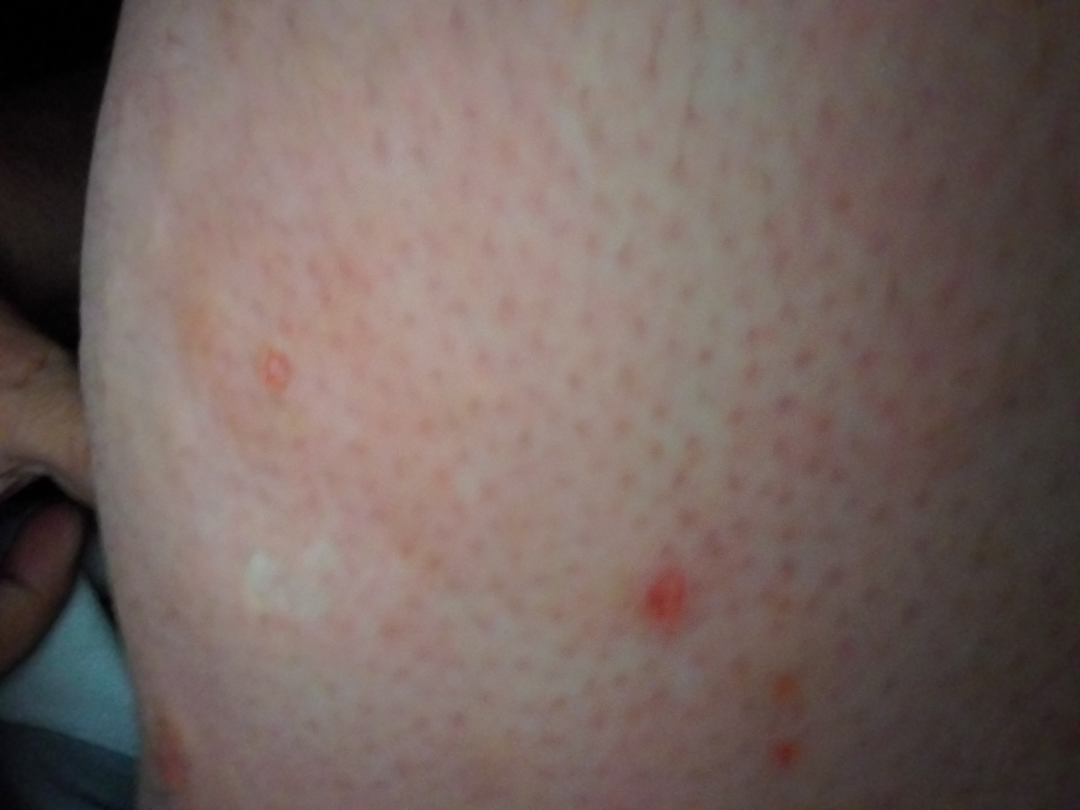Q: Where on the body?
A: leg
Q: Patient demographics?
A: female, age 40–49
Q: What is the framing?
A: close-up
Q: What is the dermatologist's impression?
A: Urticaria and Allergic Contact Dermatitis were considered with similar weight